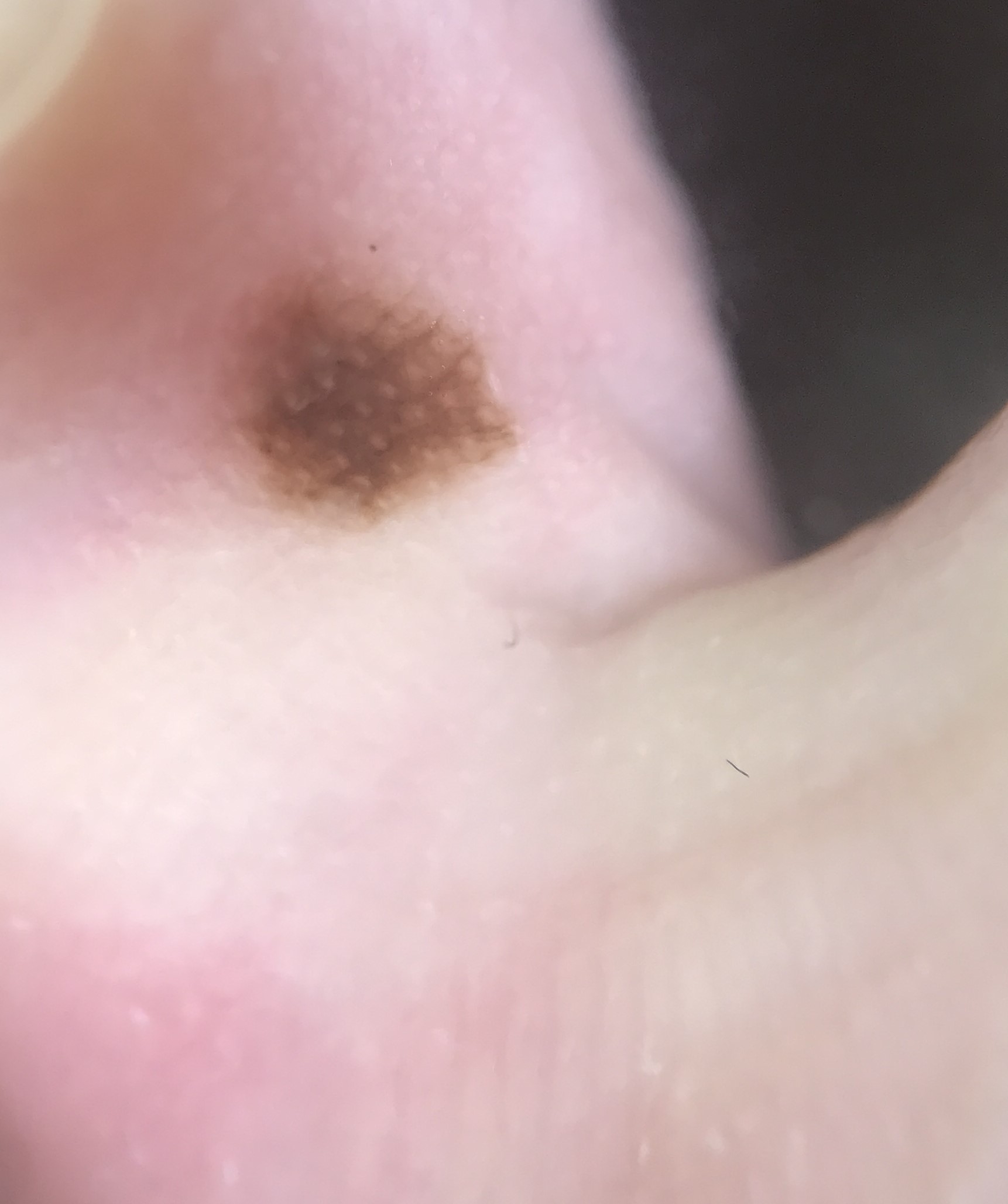{
  "image": "dermatoscopy",
  "lesion_type": {
    "main_class": "banal",
    "pattern": "junctional"
  },
  "diagnosis": {
    "name": "acral junctional nevus",
    "code": "ajb",
    "malignancy": "benign",
    "super_class": "melanocytic",
    "confirmation": "expert consensus"
  }
}